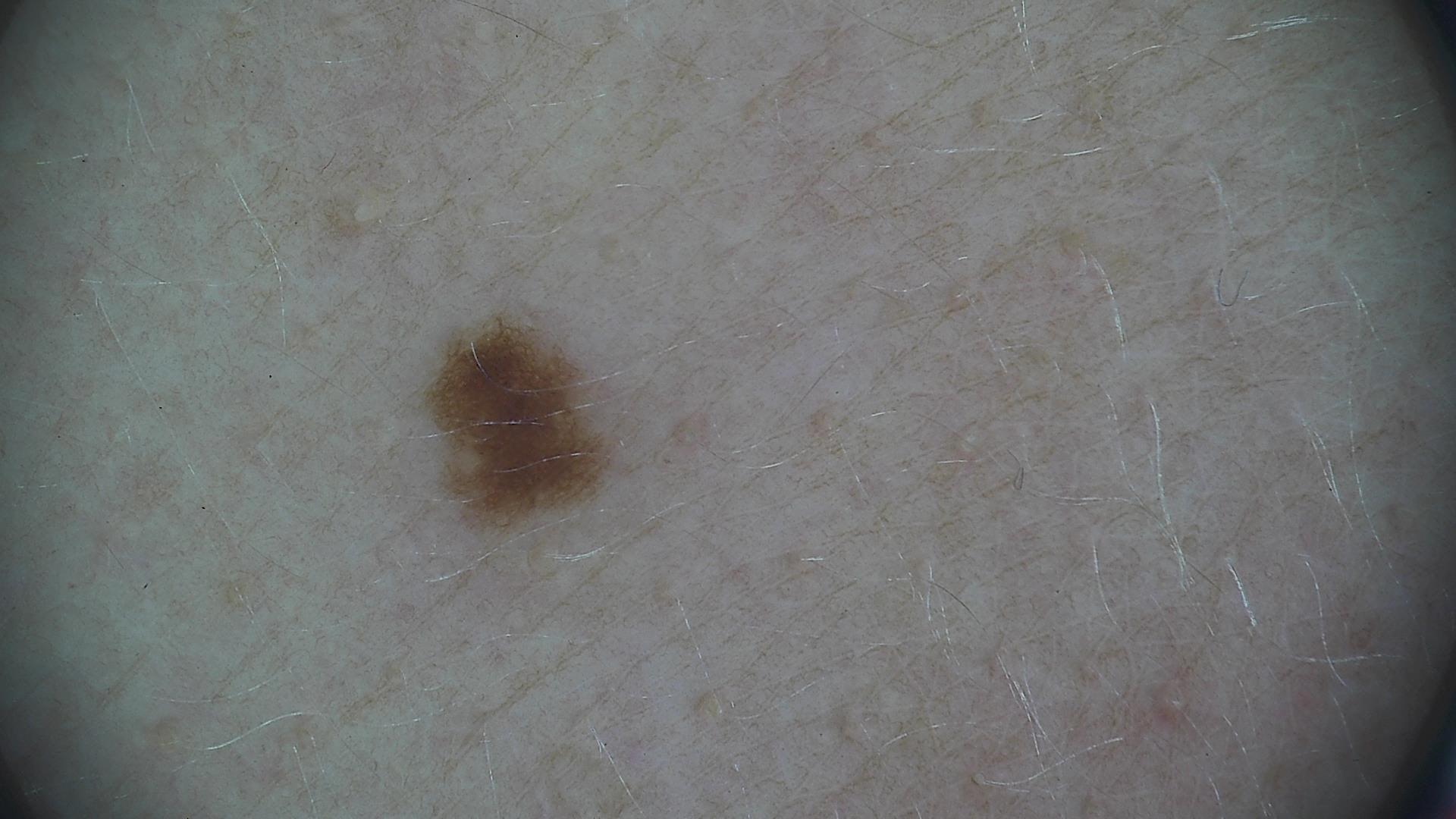label: dysplastic junctional nevus (expert consensus).